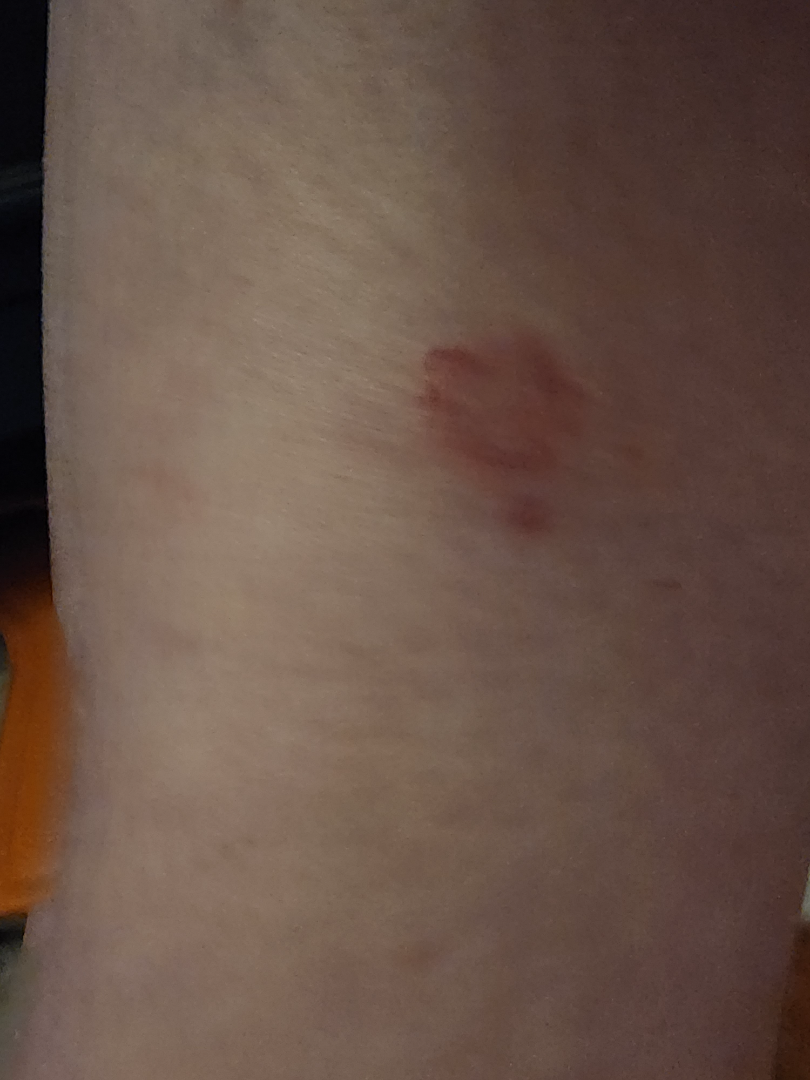shot_type: close-up
patient: female, age 50–59
body_site: leg
differential:
  tied_lead:
    - Tinea
    - Eczema
  unlikely:
    - Pityriasis rosea